The lesion is described as raised or bumpy, located on the arm, close-up view, reported duration is less than one week, the patient reports burning and itching, the patient described the issue as a rash: 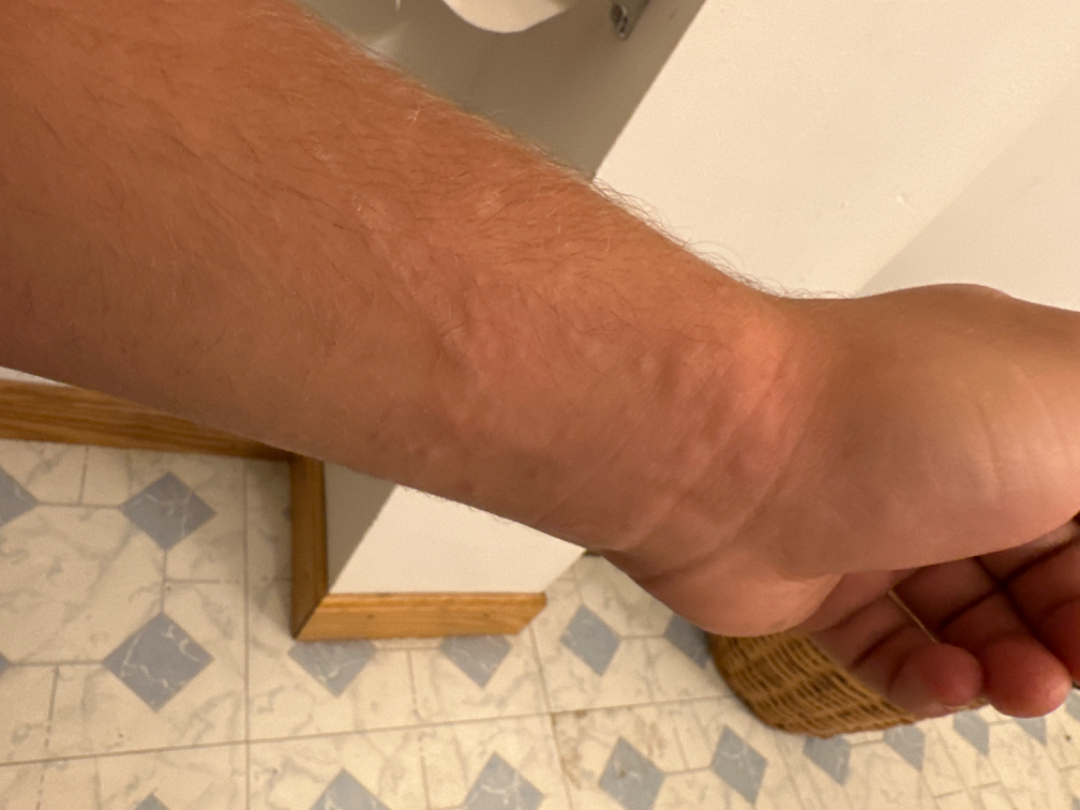Review: On photographic review by a dermatologist: the primary impression is Urticaria.